The photograph is a close-up of the affected area.
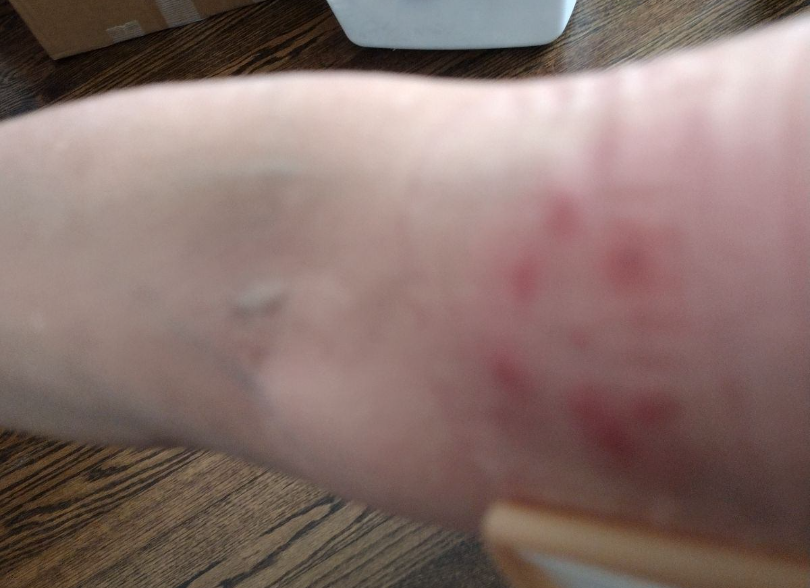Diagnostic features were not clearly distinguishable in this photograph.